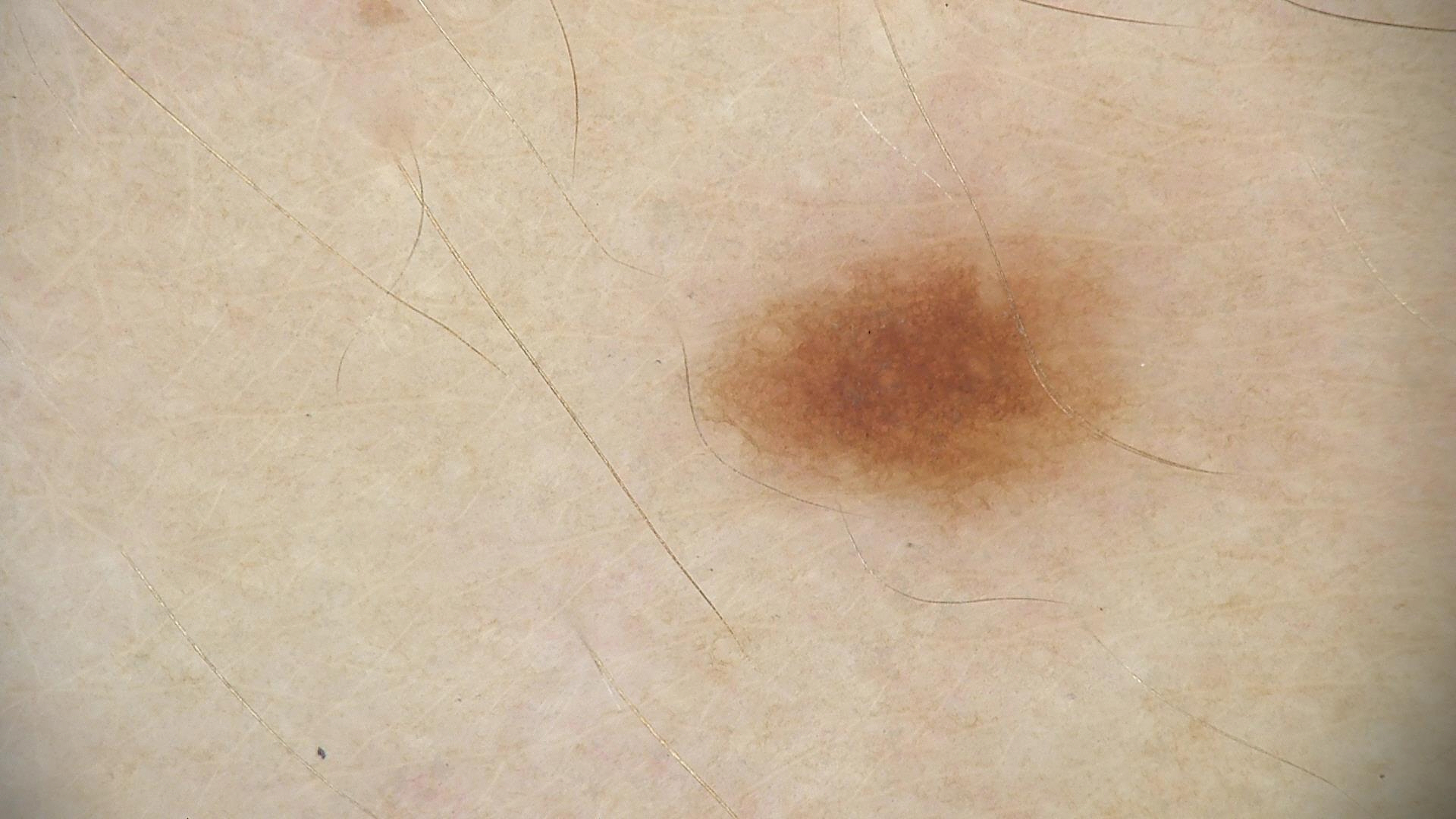A skin lesion imaged with a dermatoscope. Diagnosed as a dysplastic junctional nevus.